A dermoscopic close-up of a skin lesion:
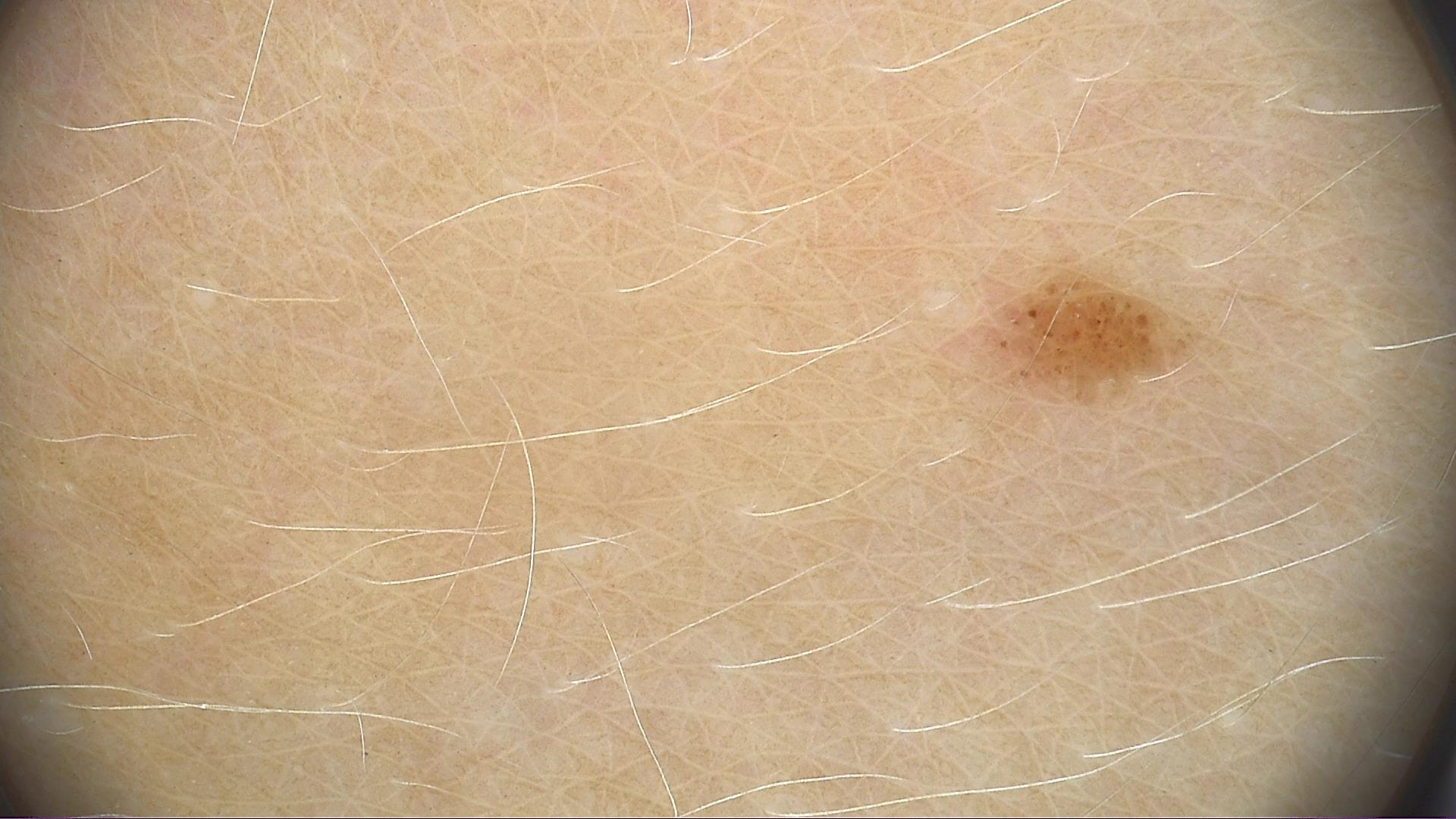Findings: The architecture is that of a banal lesion. Impression: Classified as a junctional nevus.